A male subject 39 years of age; Fitzpatrick skin type II; history notes alcohol use, pesticide exposure, no prior malignancy (patient or family), and no tobacco use:
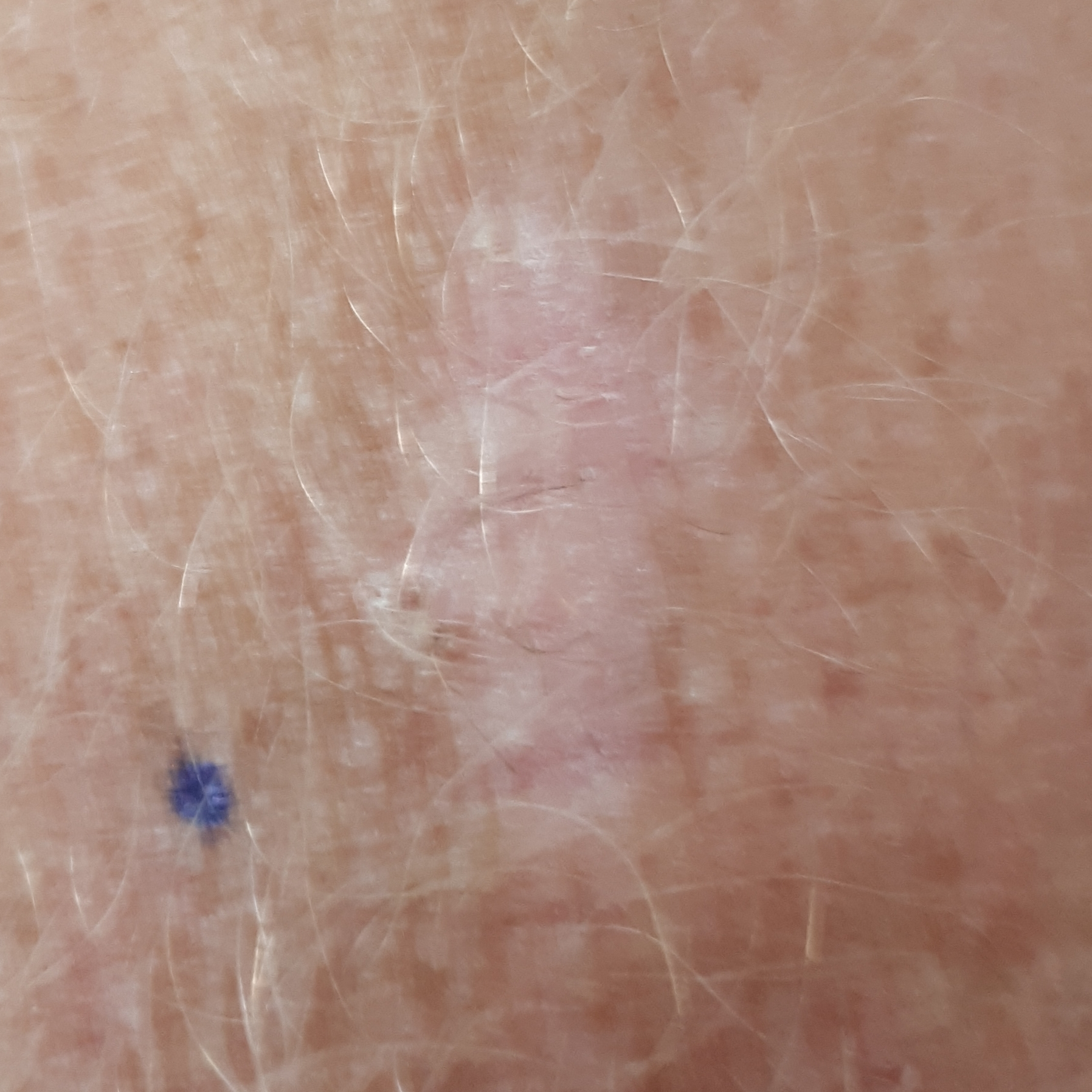The lesion was found on an arm. The lesion measures 20 × 10 mm. The patient reports no symptoms. Biopsy-confirmed as a lesion with uncertain malignant potential — an actinic keratosis.